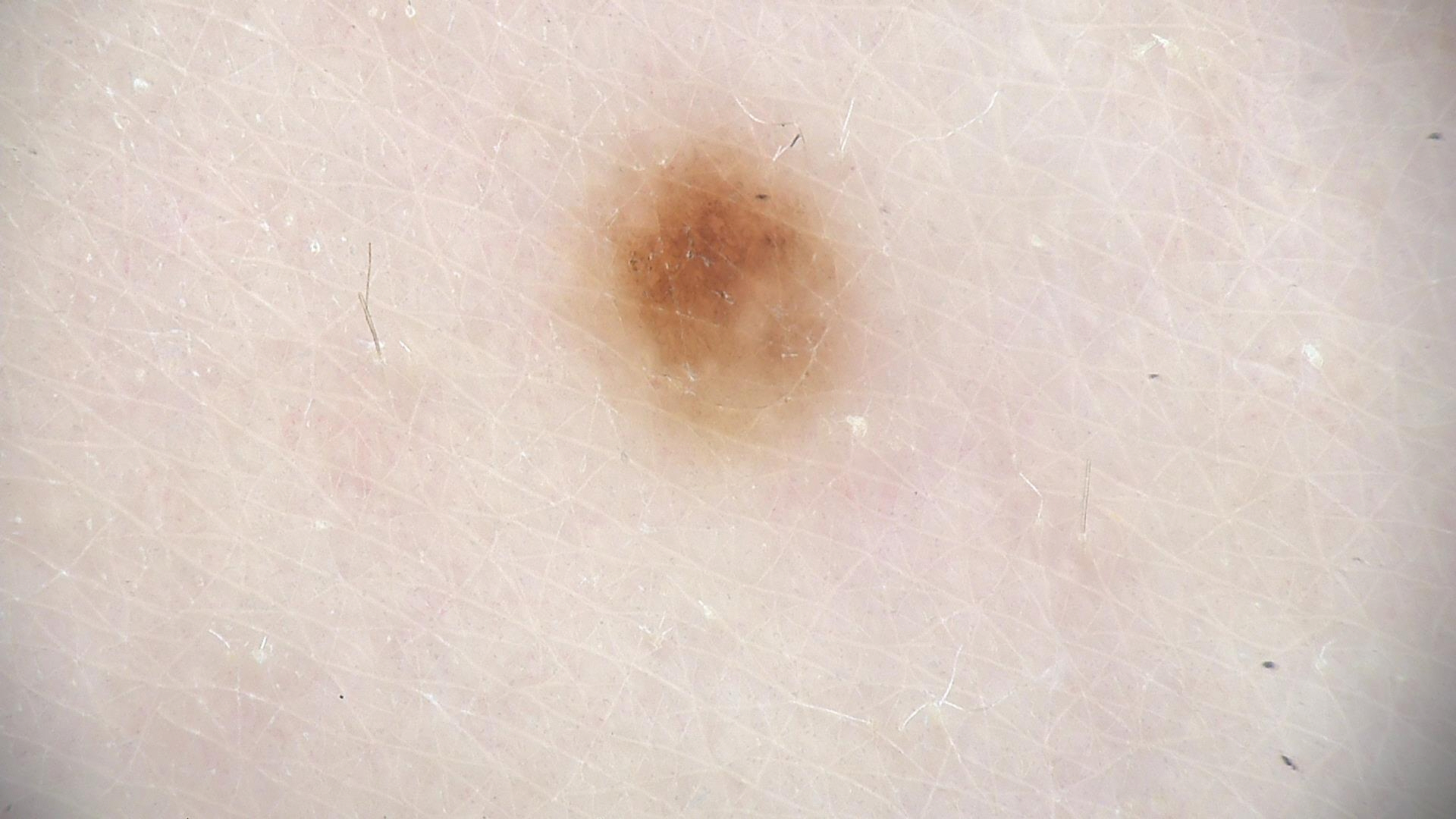A skin lesion imaged with a dermatoscope. Labeled as a benign lesion — a dysplastic junctional nevus.